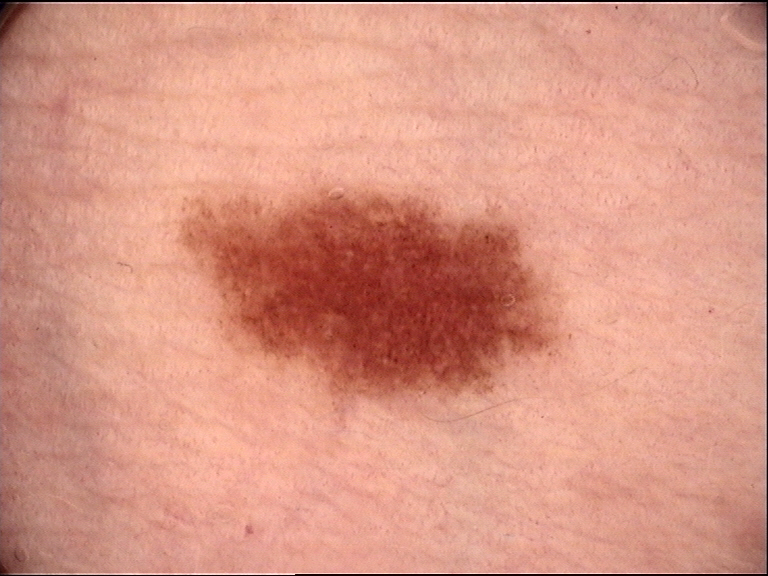class: dysplastic junctional nevus (expert consensus).